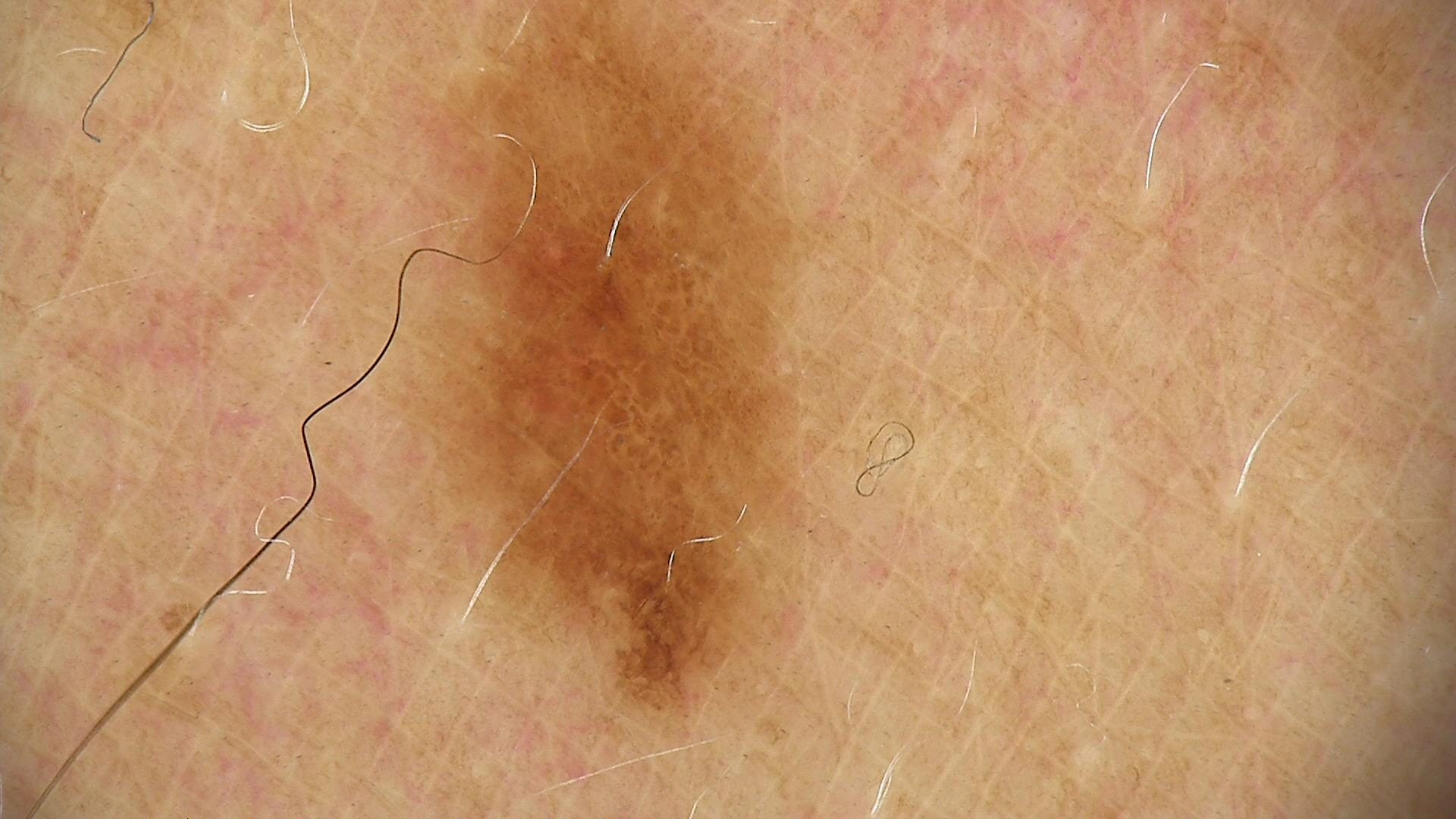Conclusion: Labeled as a dysplastic junctional nevus.